A close-up photograph:
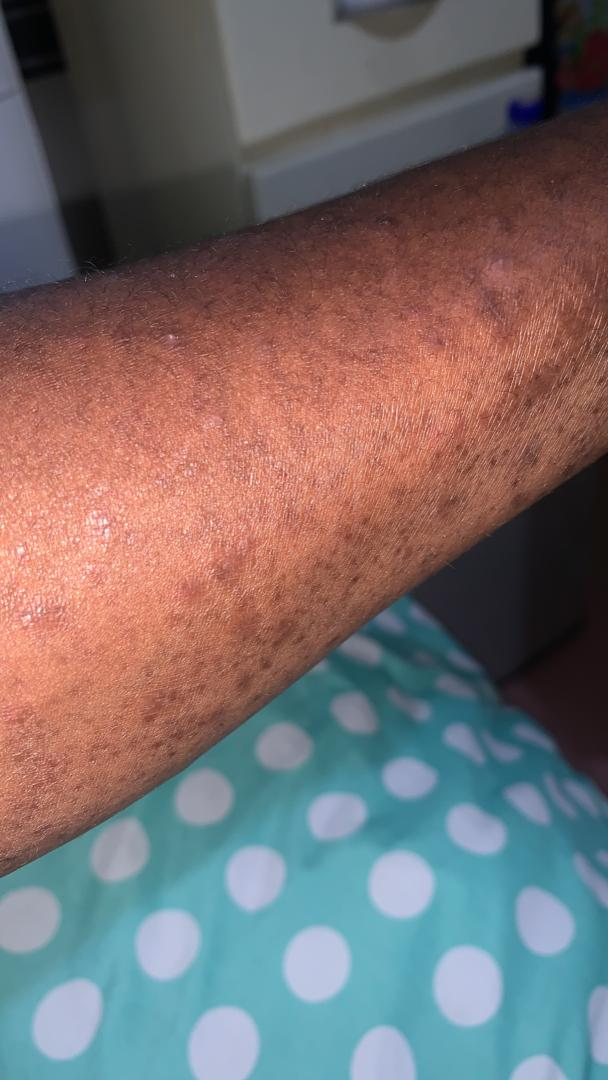Findings:
* assessment: not assessable